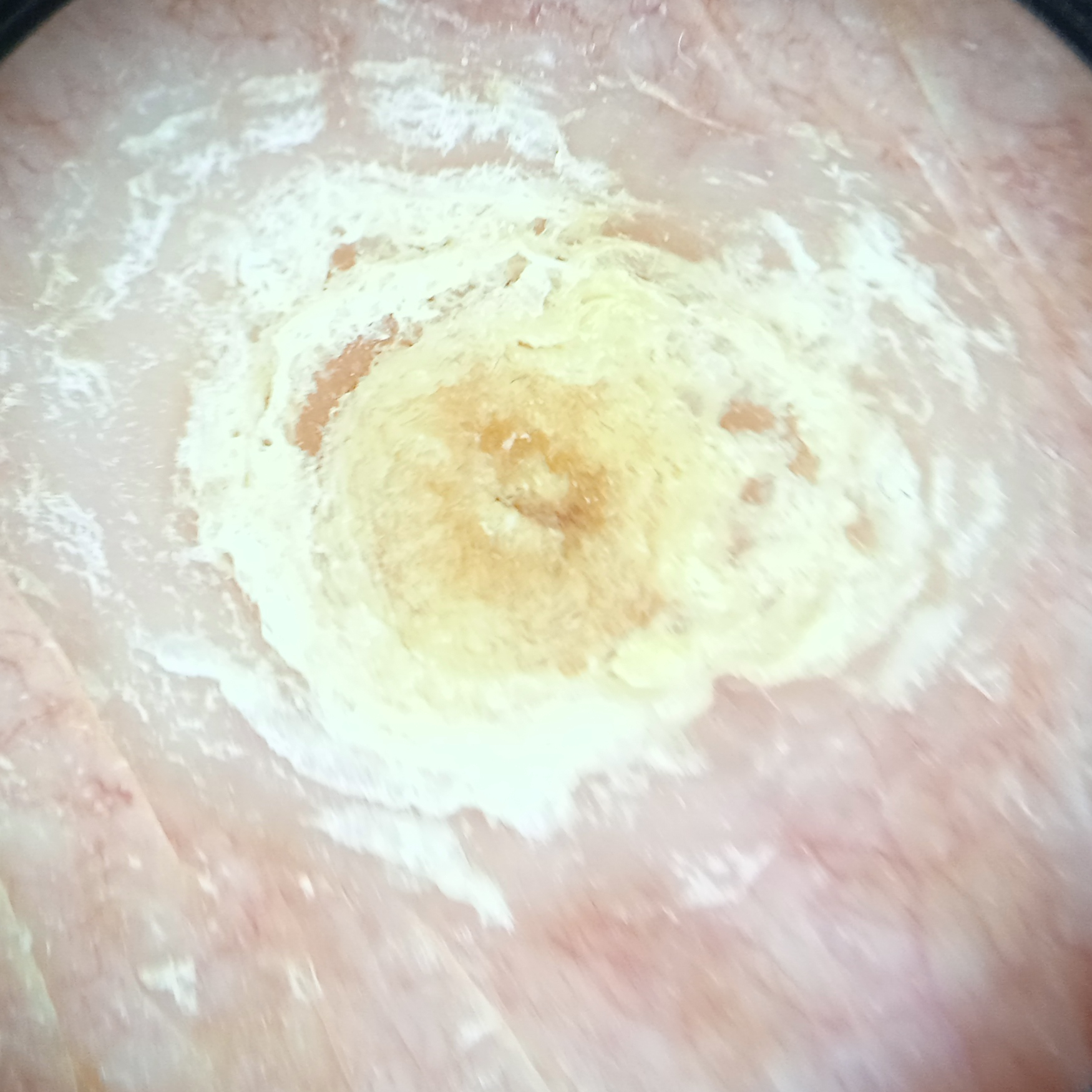A female patient 92 years old. A dermoscopy image of a skin lesion. By self-report, a family history of skin cancer and a personal history of cancer. The patient says their skin tans without first burning. Collected as part of a research study, without a referral diagnosis. The lesion involves the torso. Measuring roughly 12.5 mm. Dermatologist review favored a squamous cell carcinoma.